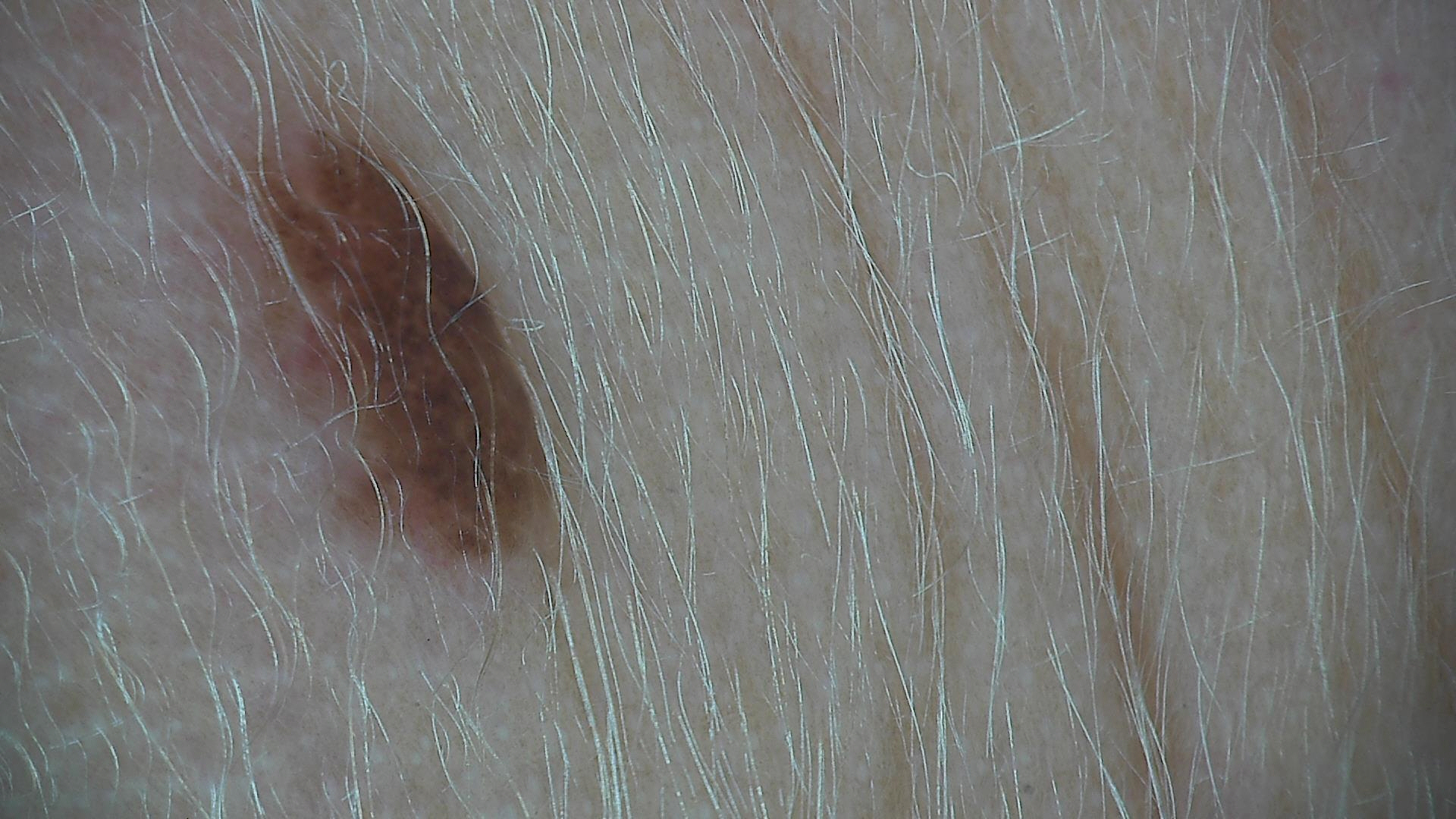A dermoscopic image of a skin lesion.
This is a banal lesion.
The diagnosis was a compound nevus.